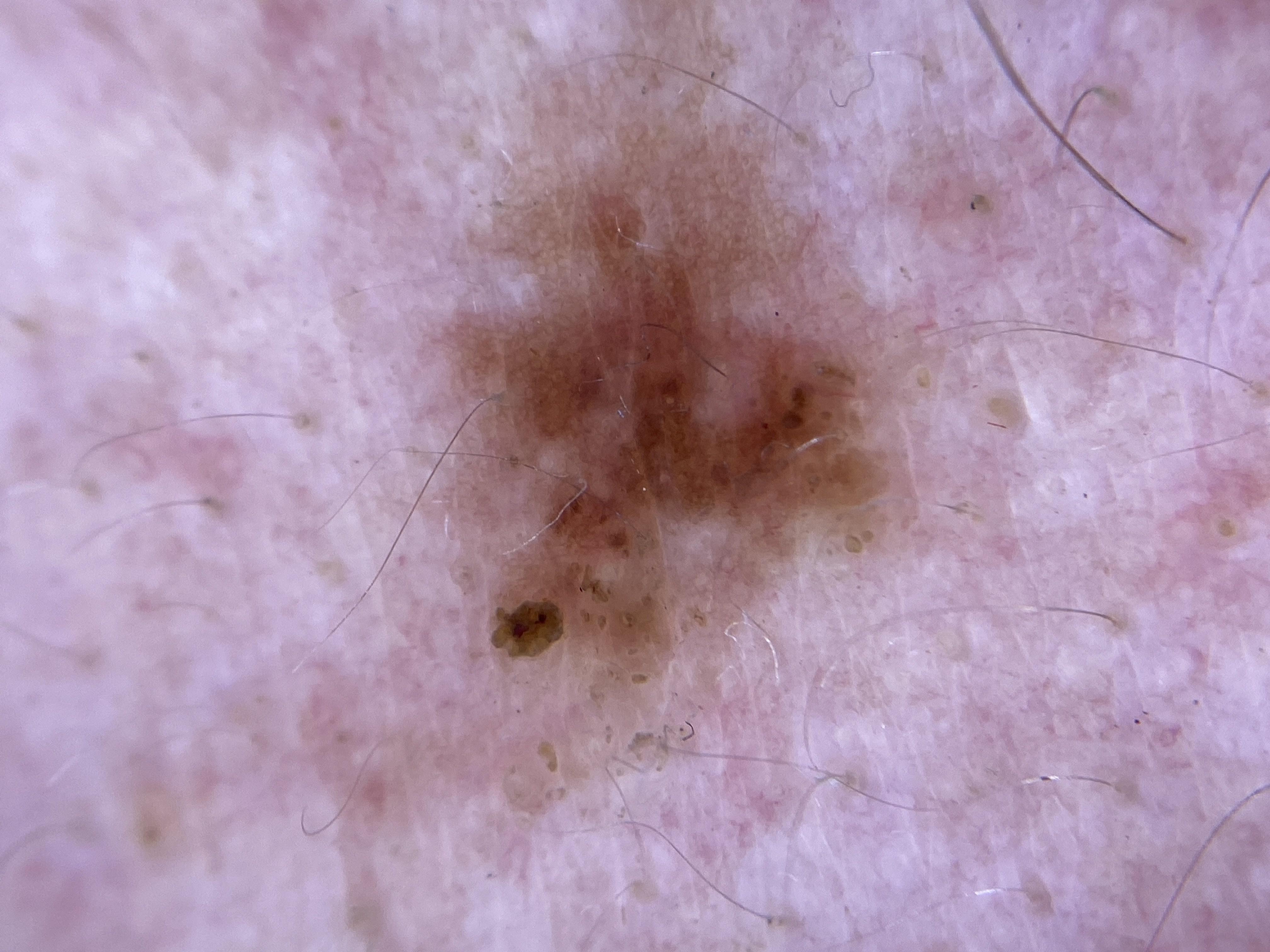Diagnosis:
Biopsy-confirmed as a nevus.